A macroscopic clinical photograph of a skin lesion. Collected as part of a research study, without a referral diagnosis. The patient says their skin tans without first burning. Few moles overall by the patient's own estimate. A male patient aged 79 — 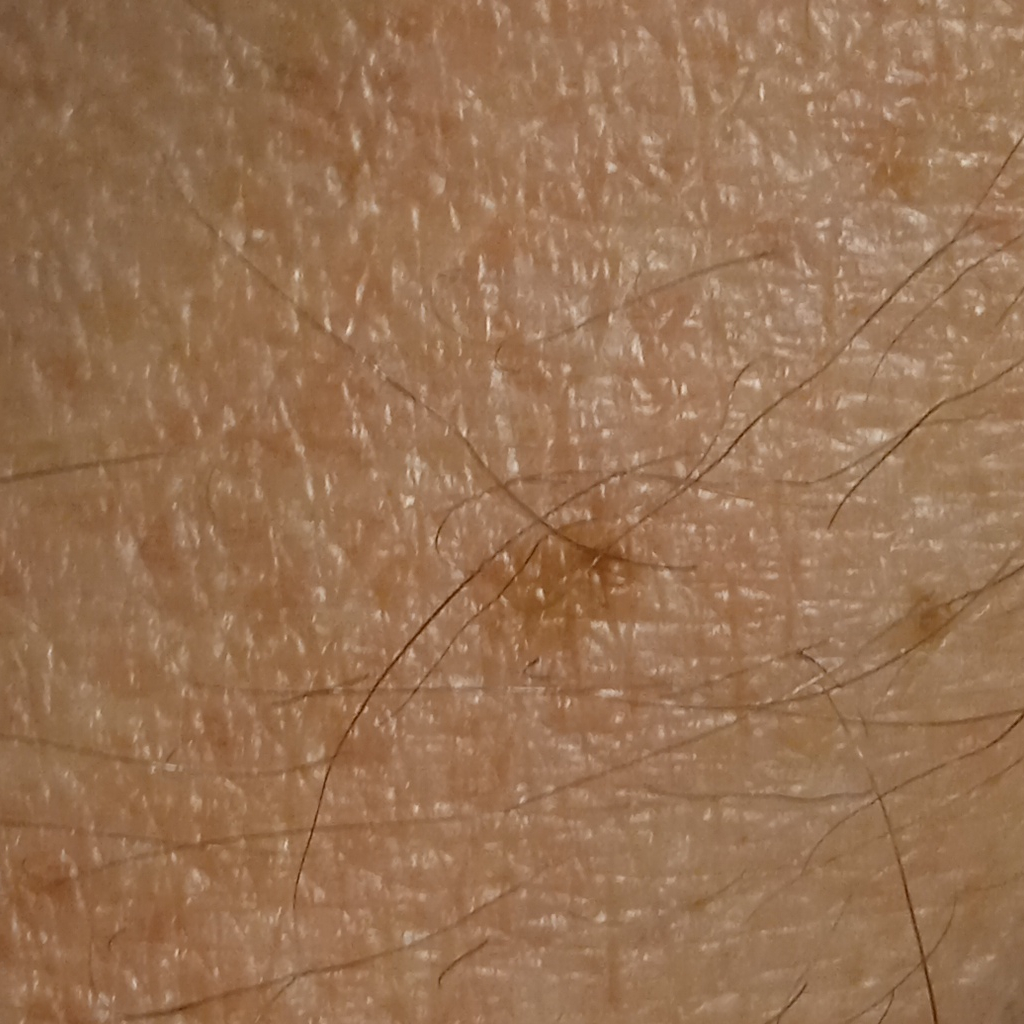site: an arm | lesion size: 4.2 mm | diagnosis: seborrheic keratosis (dermatologist consensus).